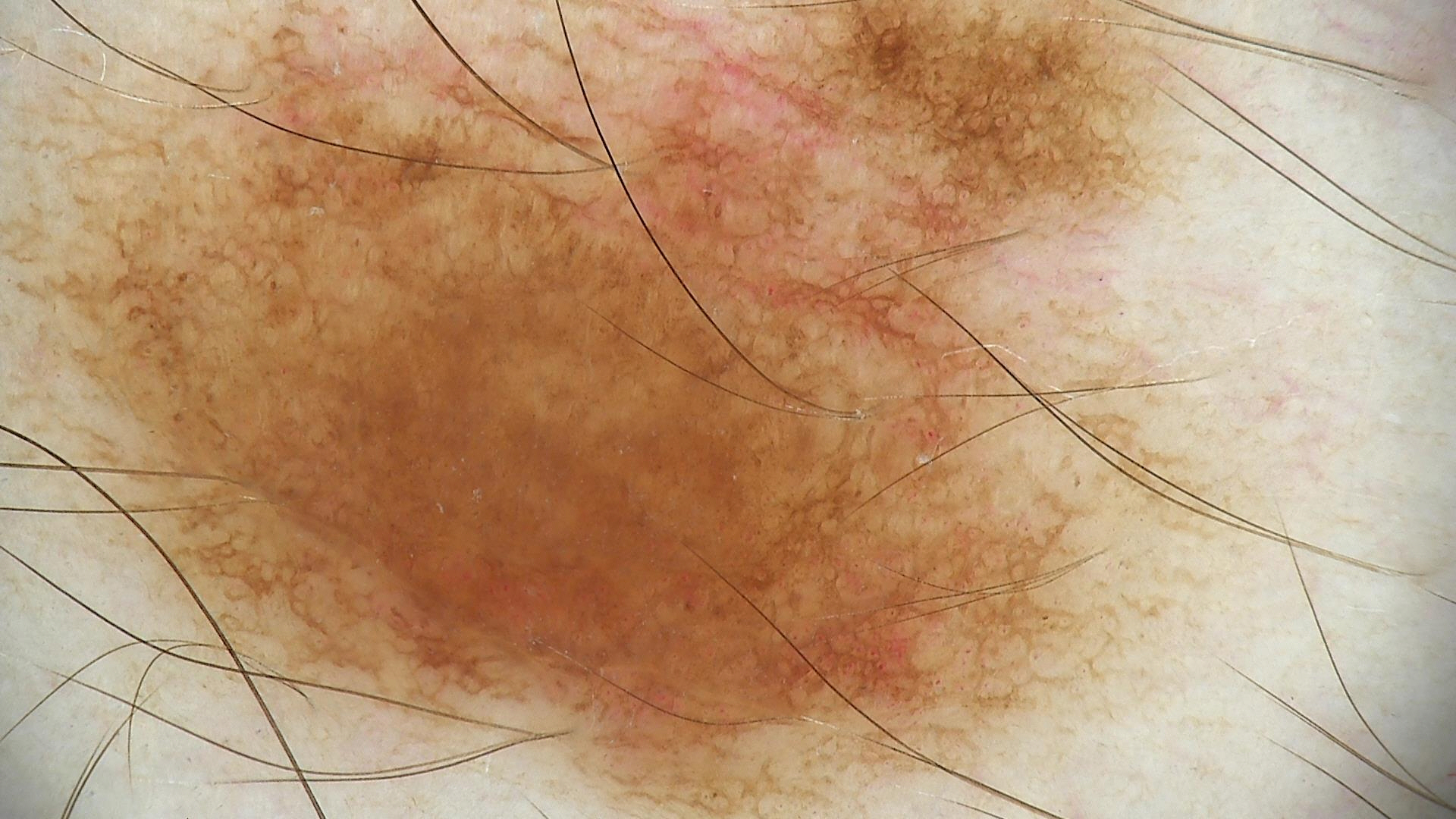| feature | finding |
|---|---|
| class | dysplastic junctional nevus (expert consensus) |